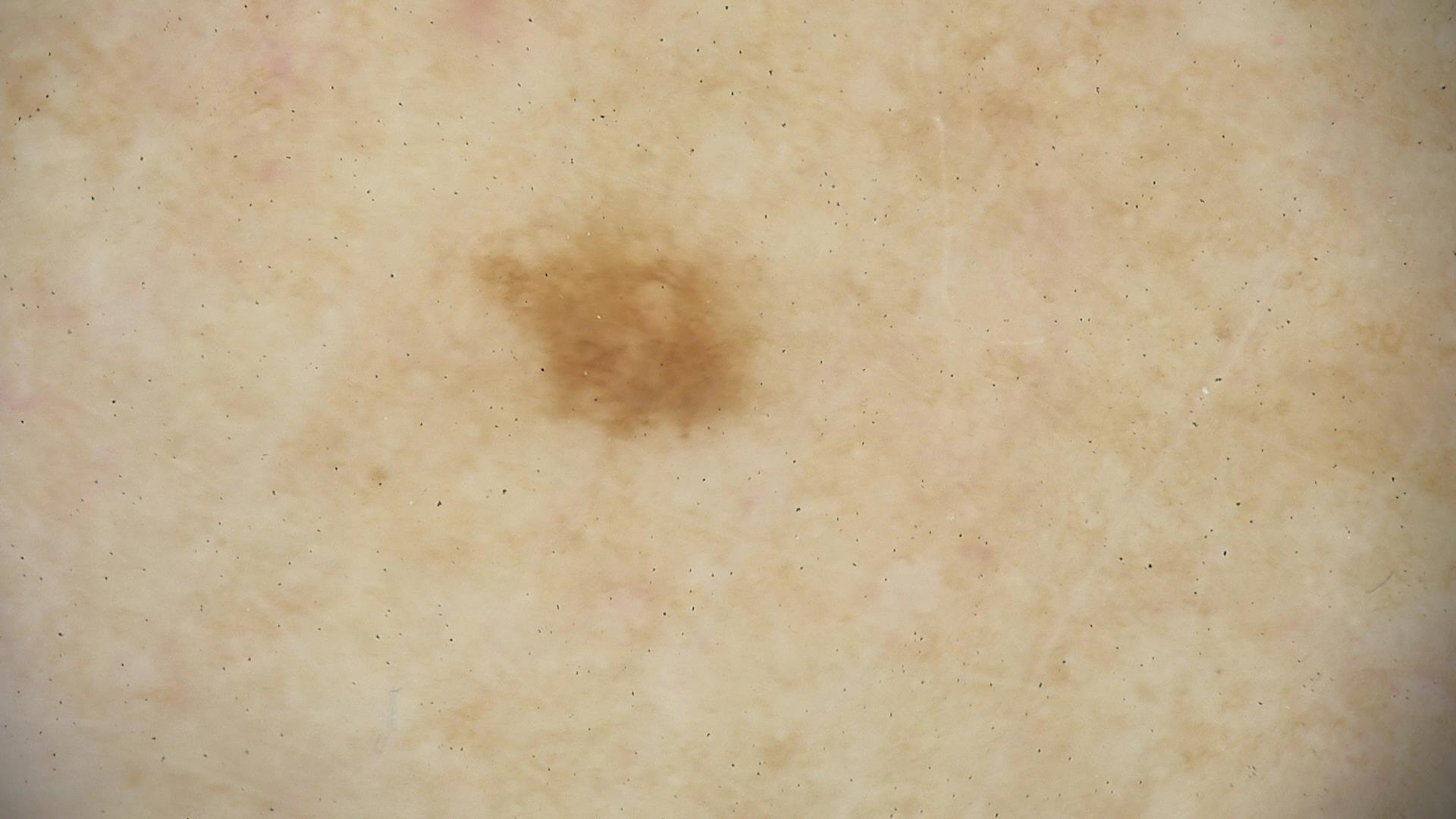A dermoscopic close-up of a skin lesion. Labeled as a benign lesion — a dysplastic junctional nevus.